A skin lesion imaged with a dermatoscope.
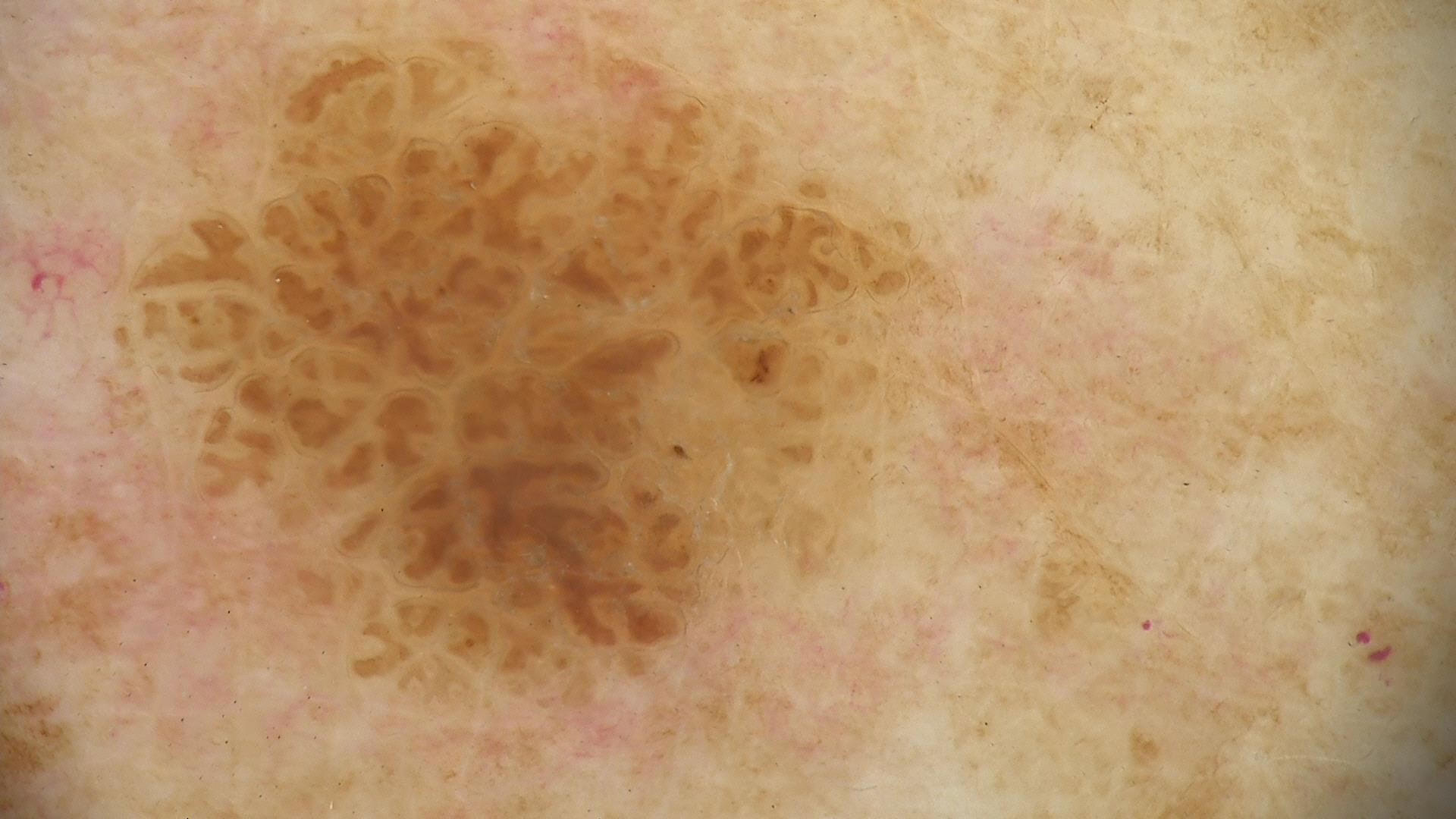This is a keratinocytic lesion. The diagnostic label was a seborrheic keratosis.